A male patient roughly 60 years of age — 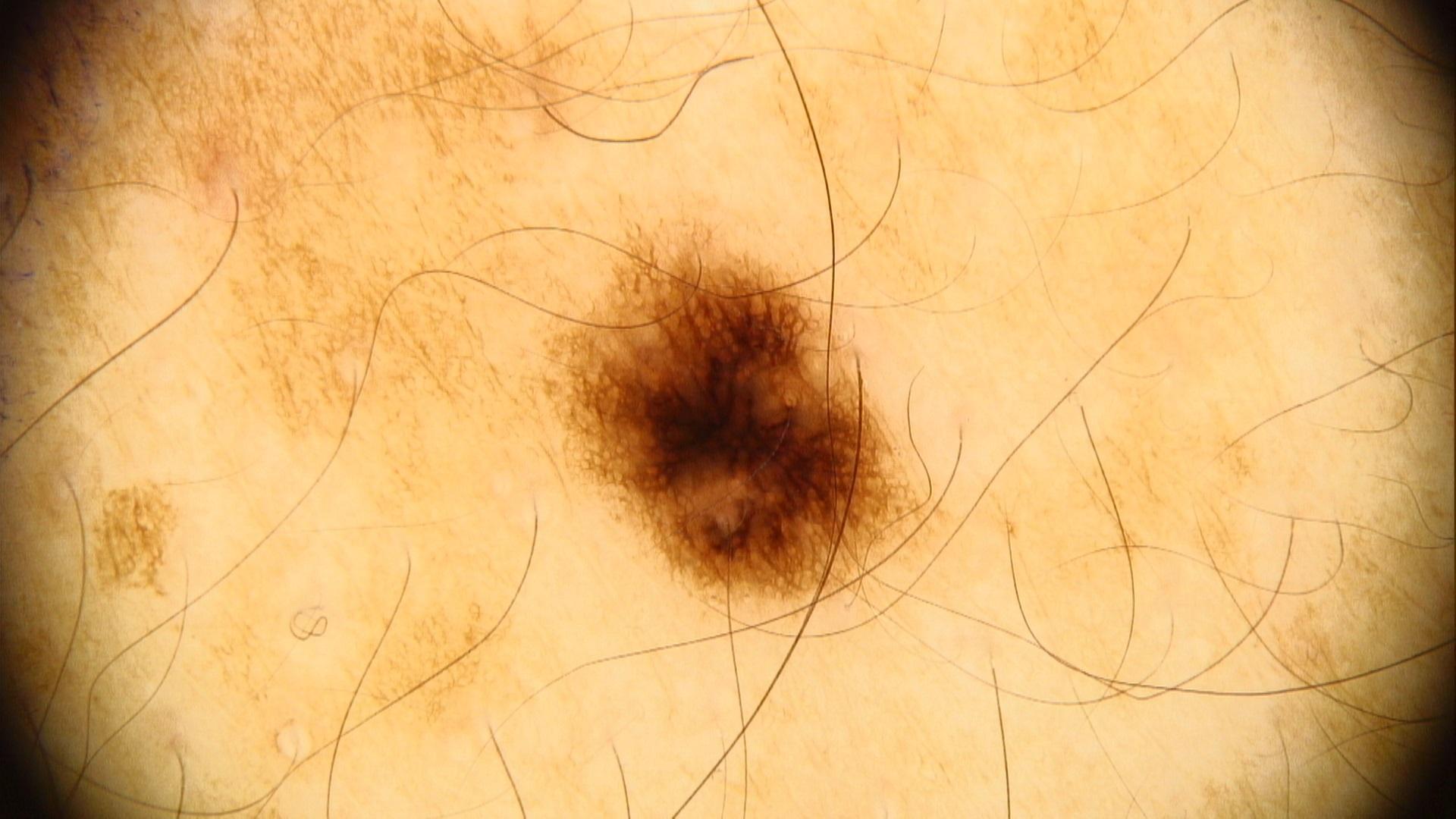<lesion>
  <diagnosis>
    <name>Nevus</name>
    <malignancy>benign</malignancy>
    <confirmation>expert clinical impression</confirmation>
    <lineage>melanocytic</lineage>
  </diagnosis>
</lesion>